This is a close-up image.
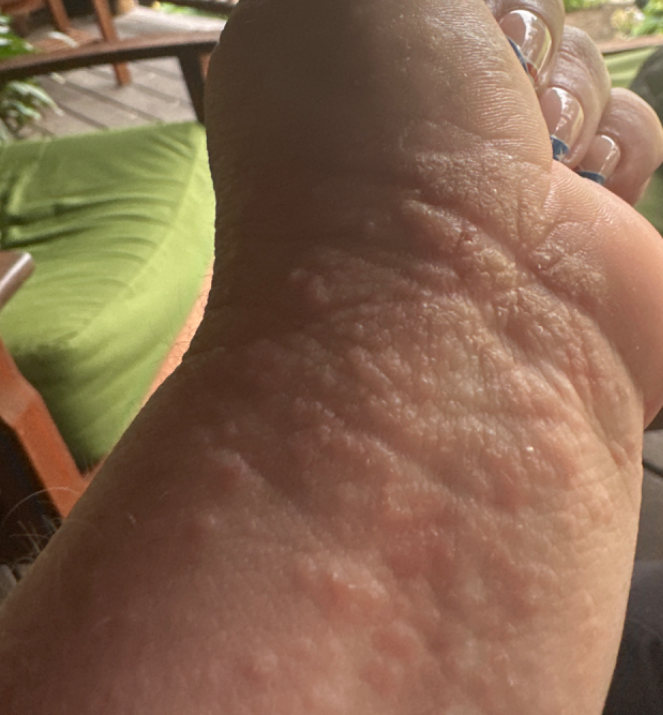The leading consideration is Allergic Contact Dermatitis; possibly Eczema.